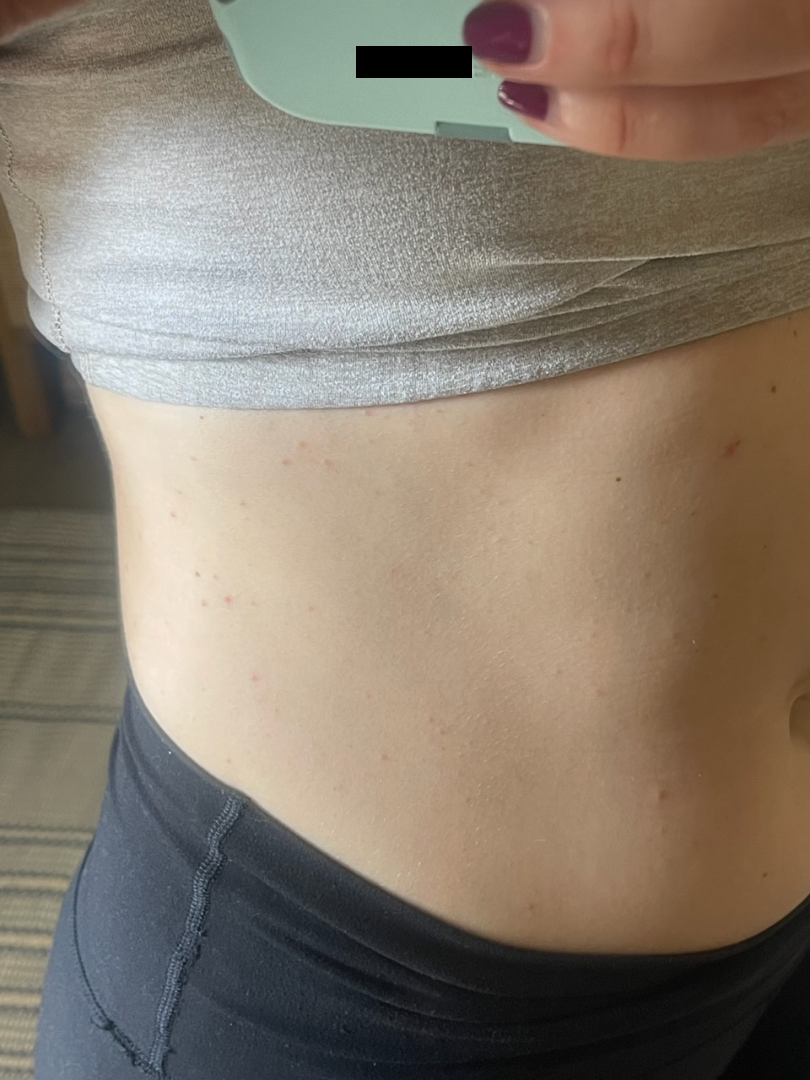The skin findings could not be characterized from the image. The arm, head or neck and front of the torso are involved. An image taken at a distance.